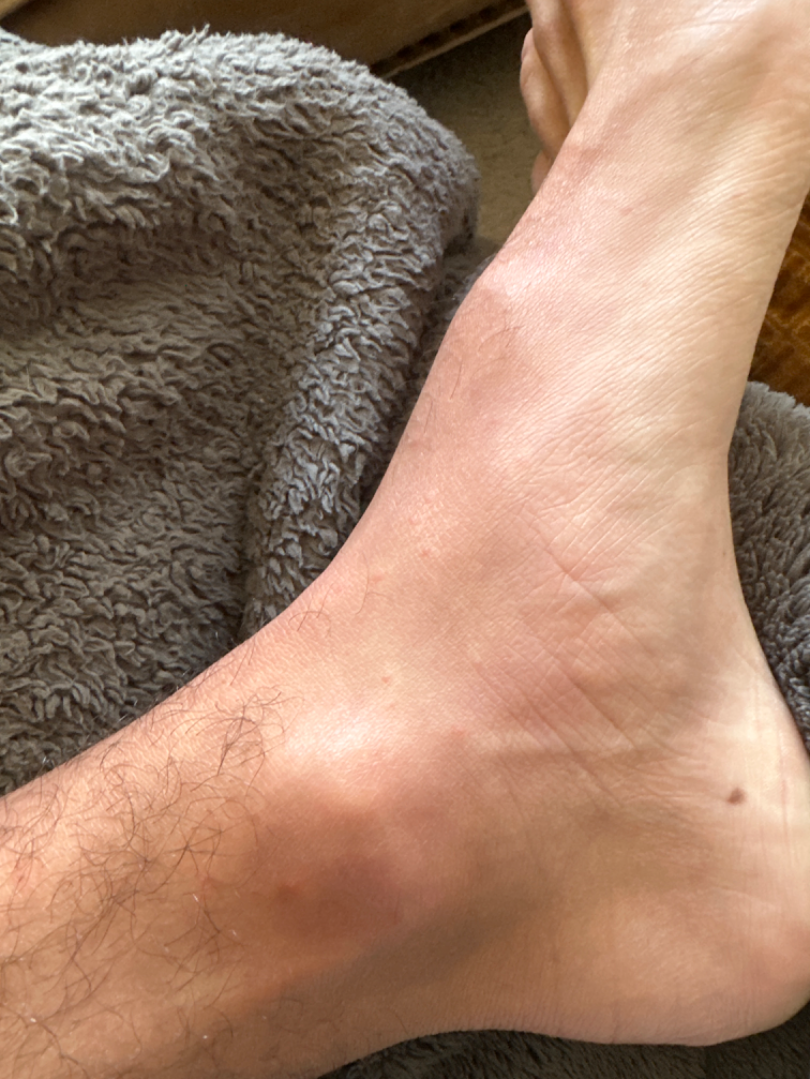No differential diagnosis could be assigned on photographic review.